A close-up photograph — 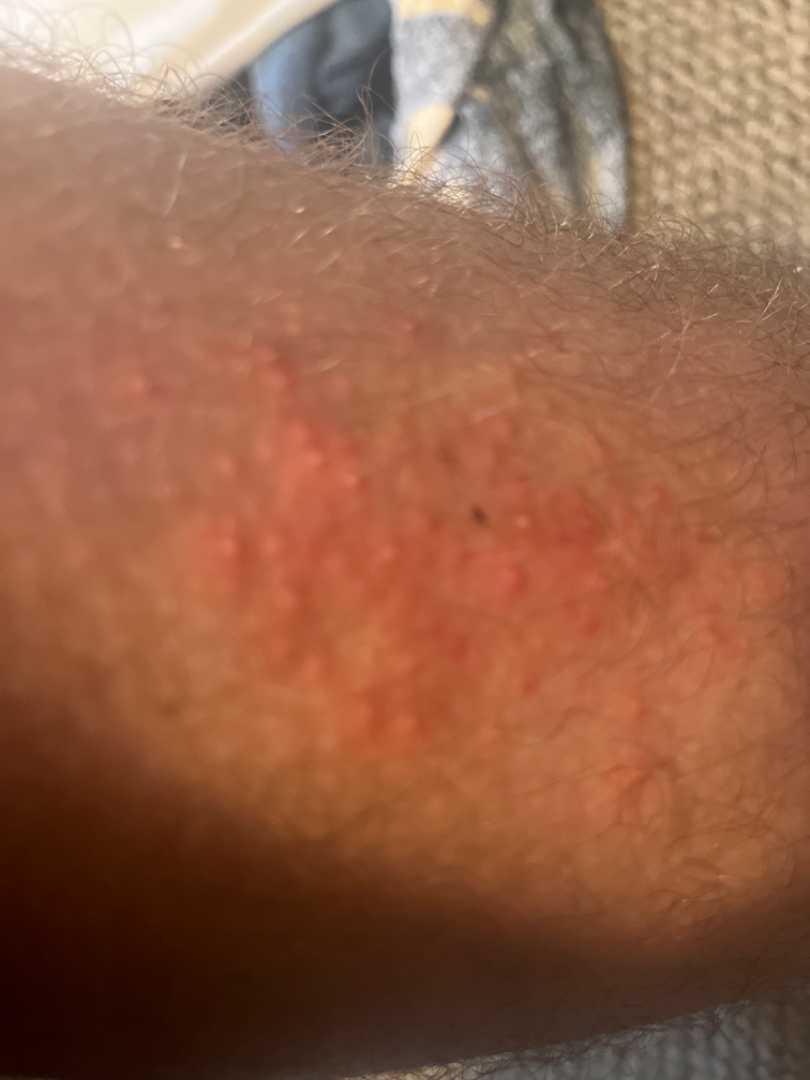The reviewer was unable to grade this case for skin condition.